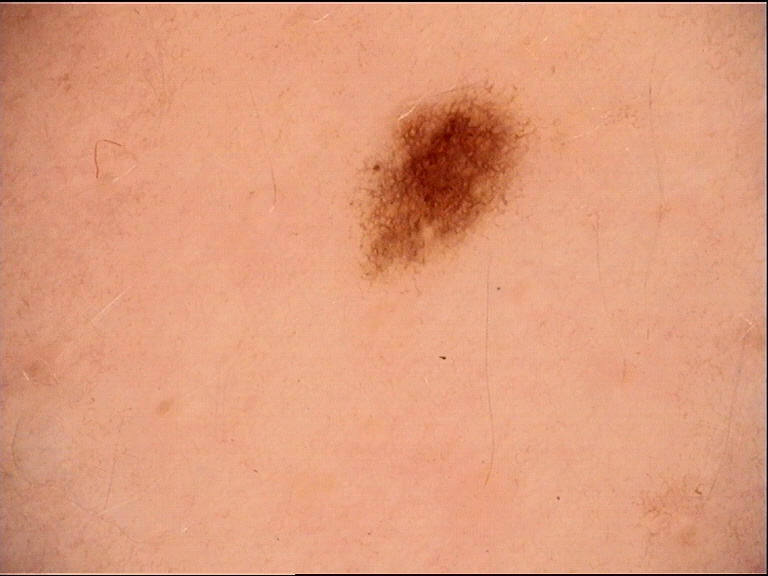Diagnosed as a benign lesion — a dysplastic junctional nevus.